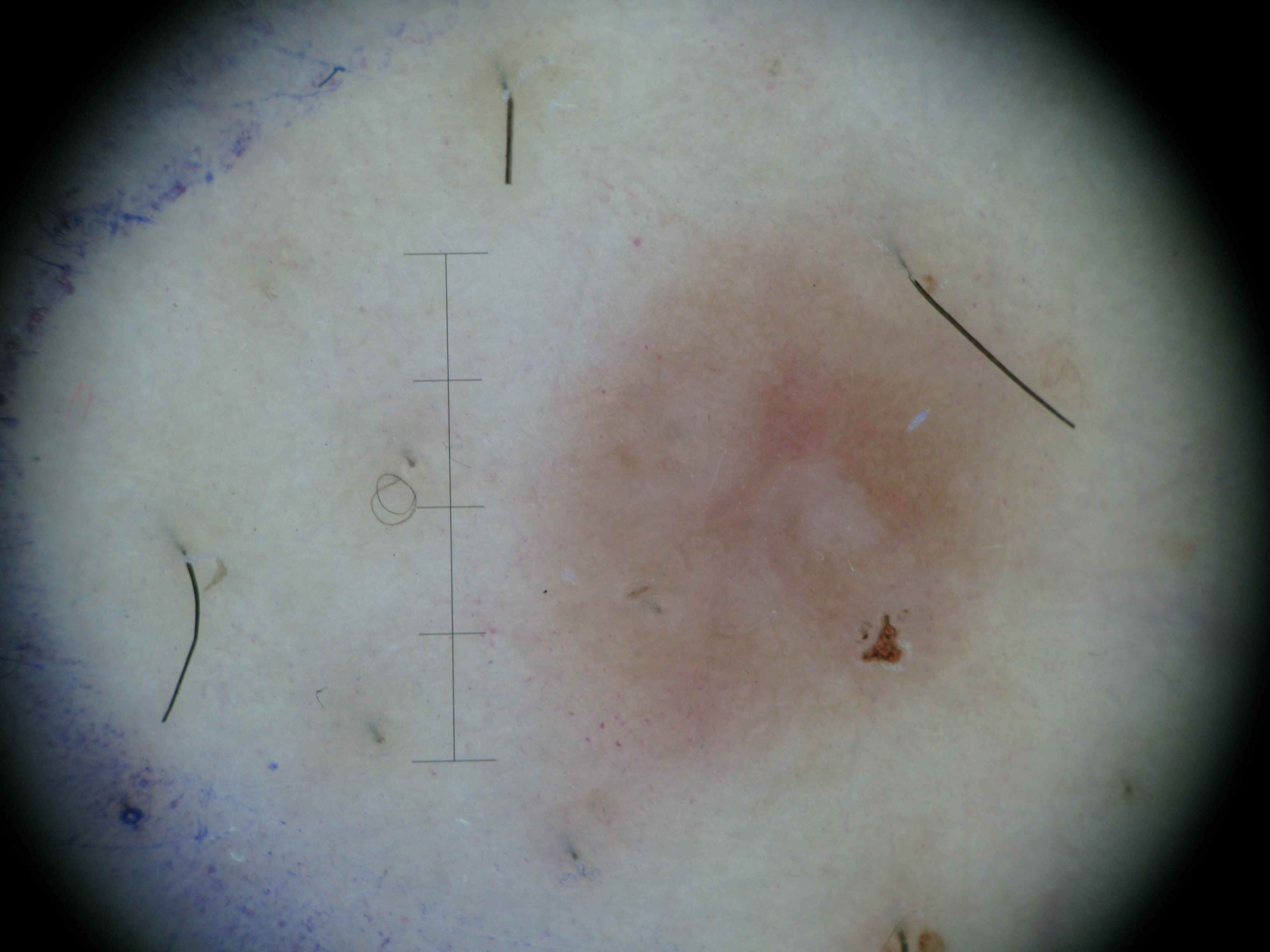The diagnostic label was a fibro-histiocytic lesion — a dermatofibroma.